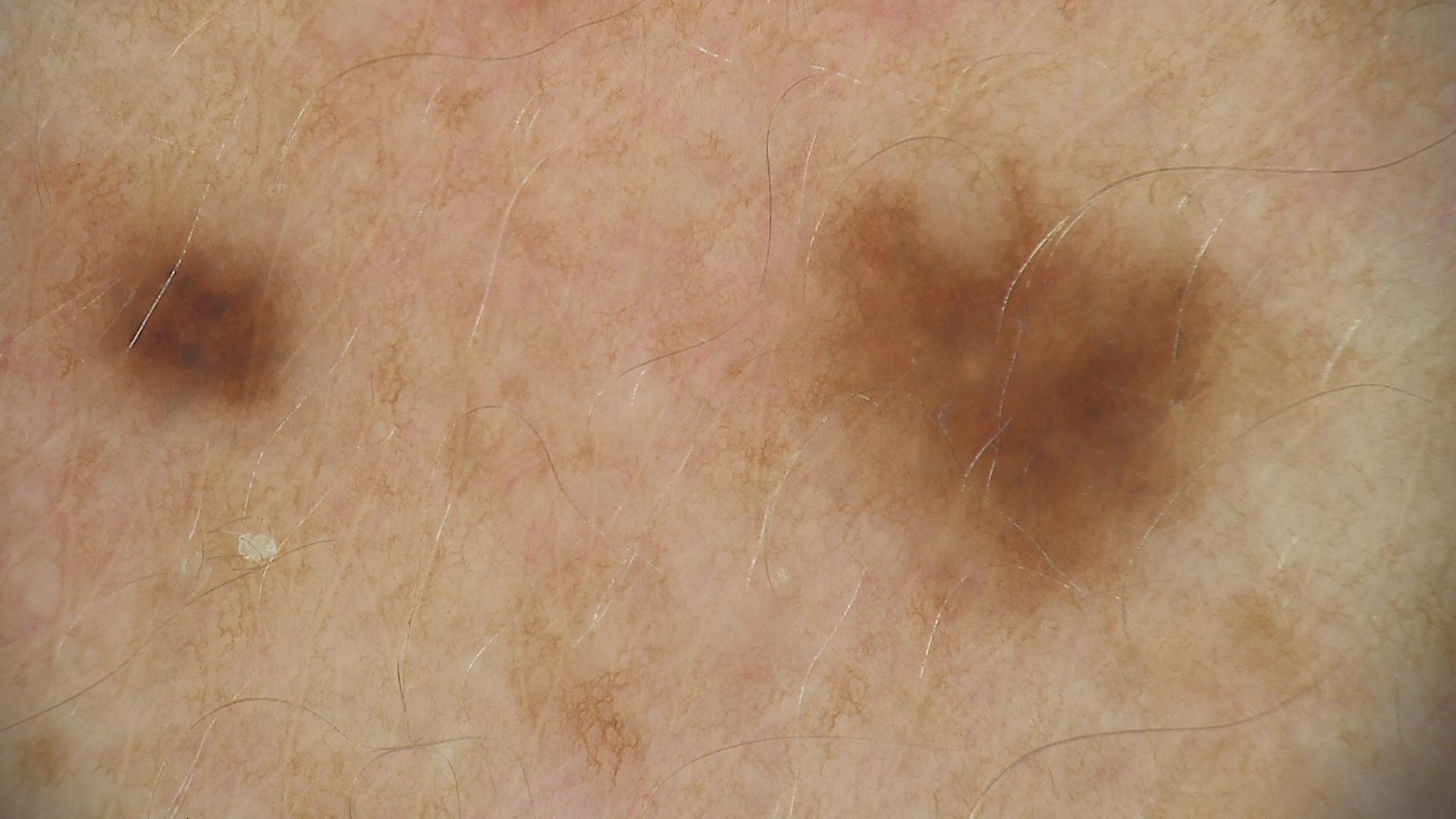Case:
A dermatoscopic image of a skin lesion.
Conclusion:
Labeled as a dysplastic junctional nevus.